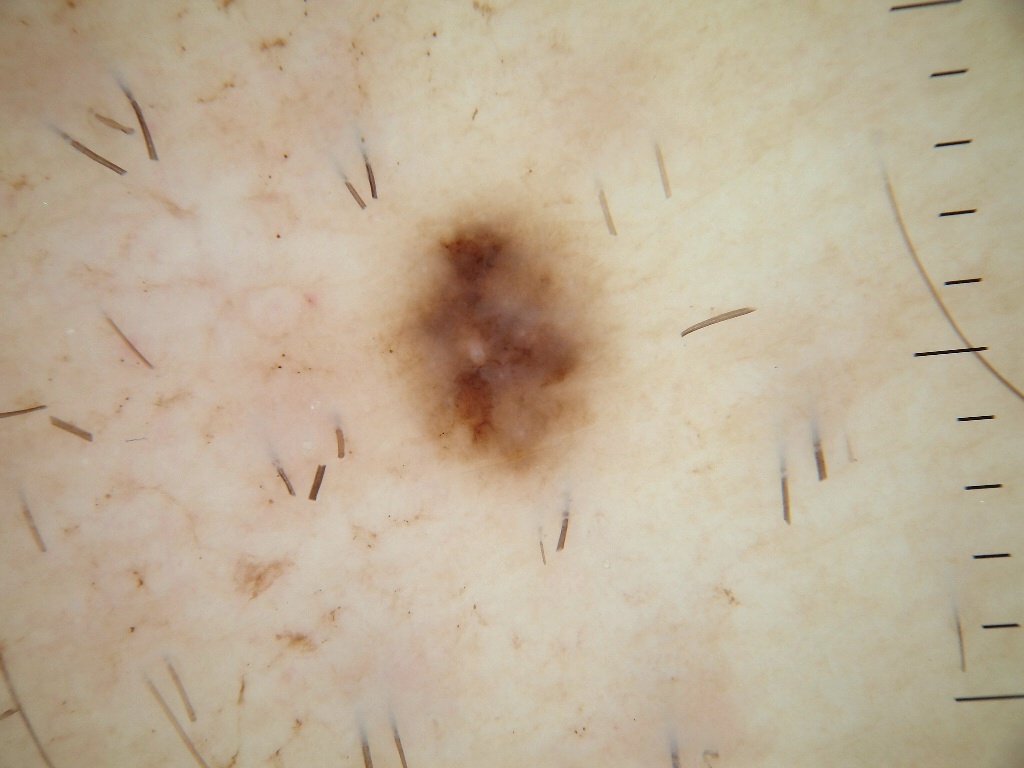The subject is a male roughly 45 years of age. Dermoscopy of a skin lesion. As (left, top, right, bottom), the lesion occupies the region <box>368, 186, 630, 504</box>. Dermoscopy demonstrates globules; no negative network, streaks, milia-like cysts, or pigment network. Expert review diagnosed this as a melanocytic nevus, a benign skin lesion.